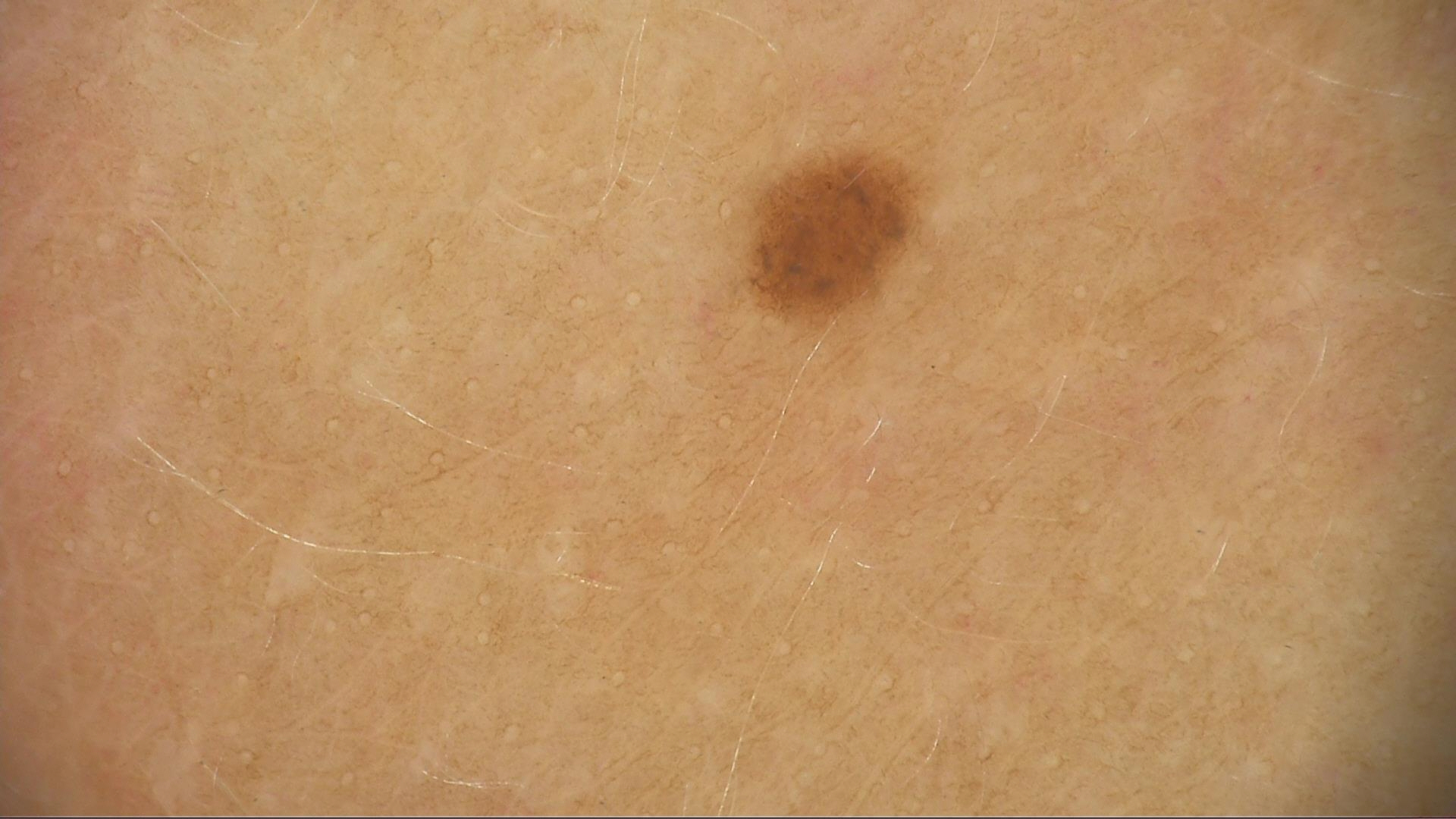imaging: dermoscopy, diagnosis: dysplastic junctional nevus (expert consensus).